A dermoscopic close-up of a skin lesion; a male patient about 45 years old: 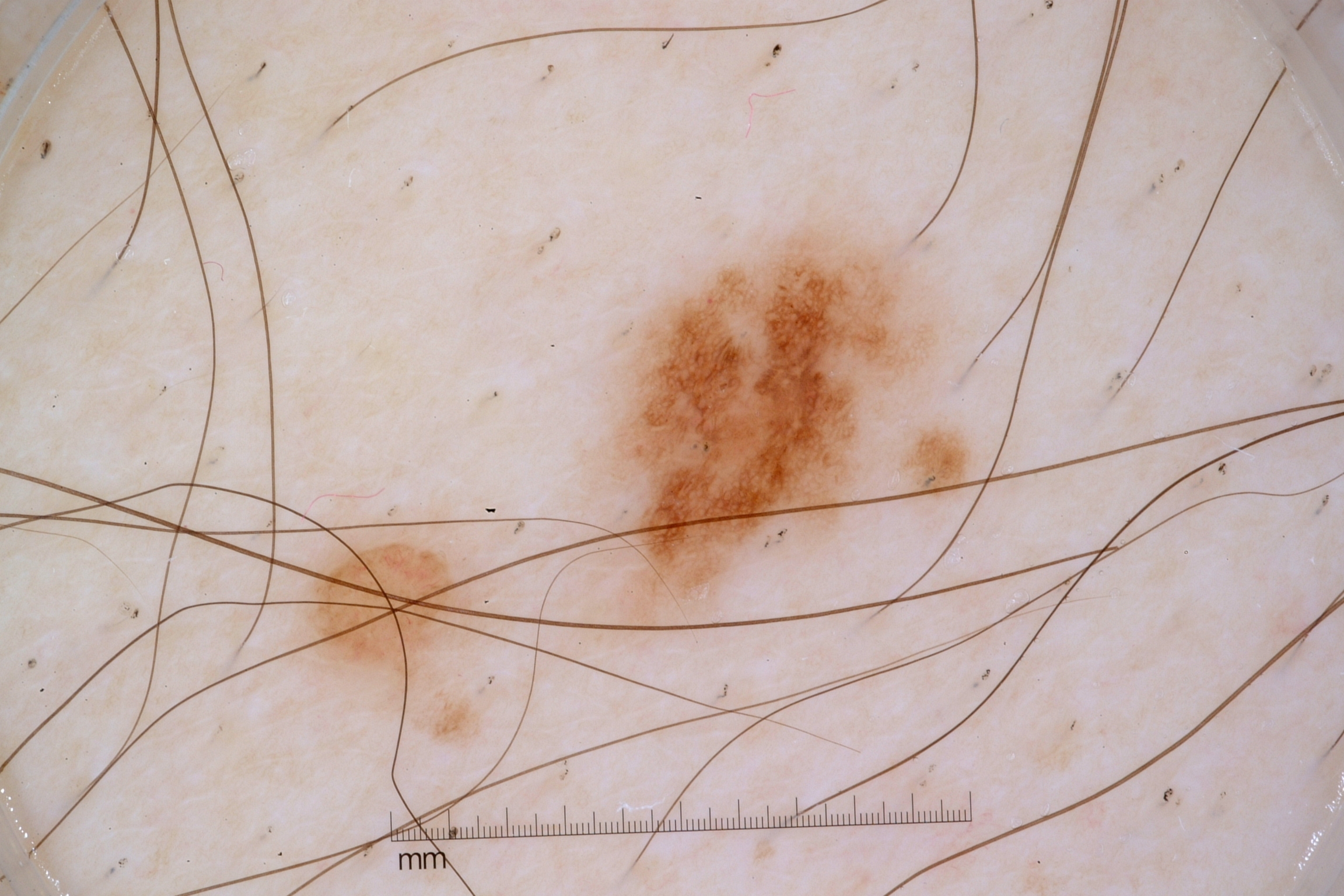  dermoscopic_features:
    present:
      - milia-like cysts
      - pigment network
    absent:
      - streaks
      - negative network
  lesion_location:
    bbox_xyxy:
      - 609
      - 232
      - 933
      - 580
  lesion_extent: small
  diagnosis:
    name: melanocytic nevus
    malignancy: benign
    lineage: melanocytic
    provenance: clinical